A skin lesion imaged with a dermatoscope:
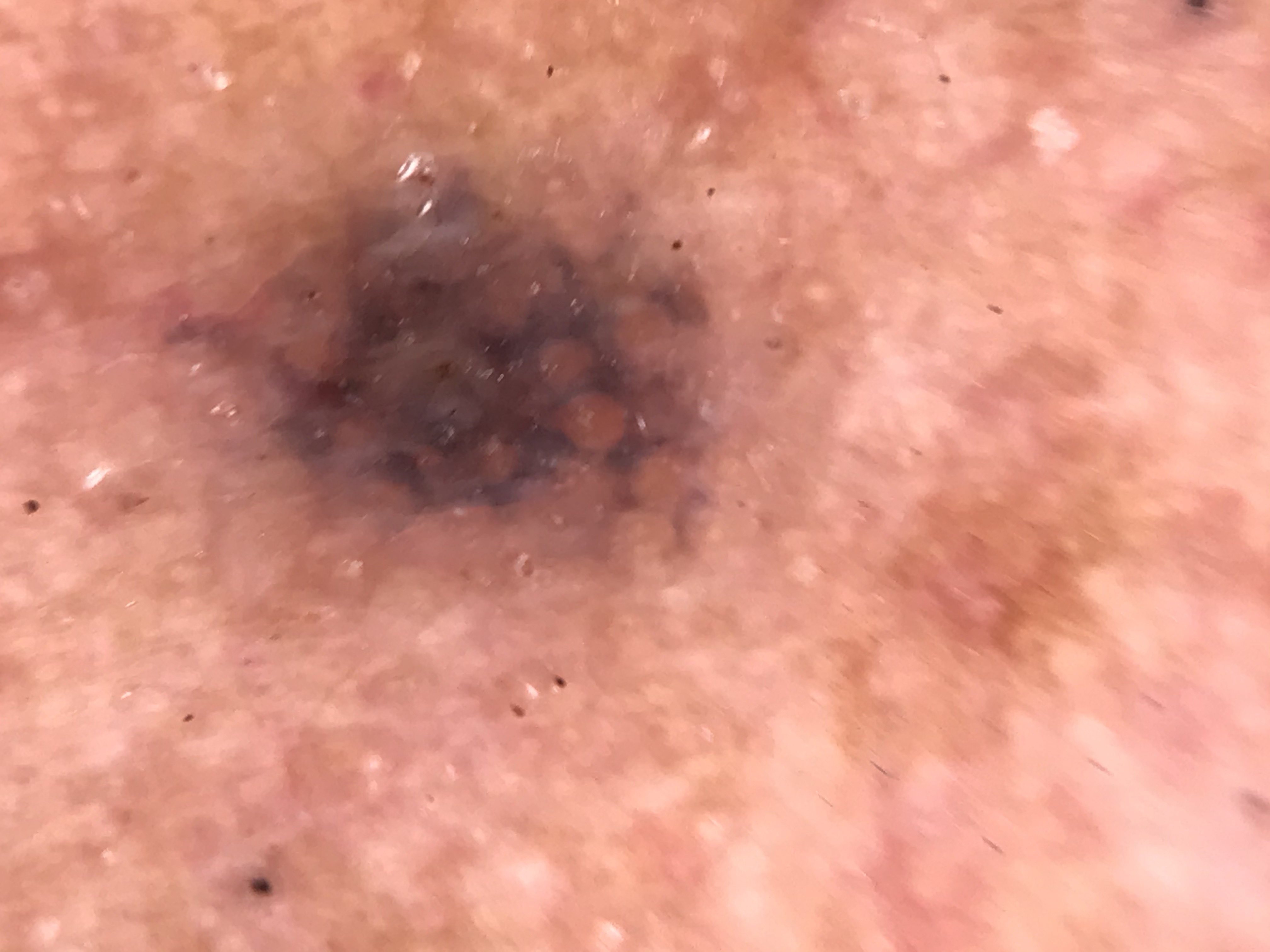The architecture is that of a banal, compound lesion.
Diagnosed as a Miescher nevus.